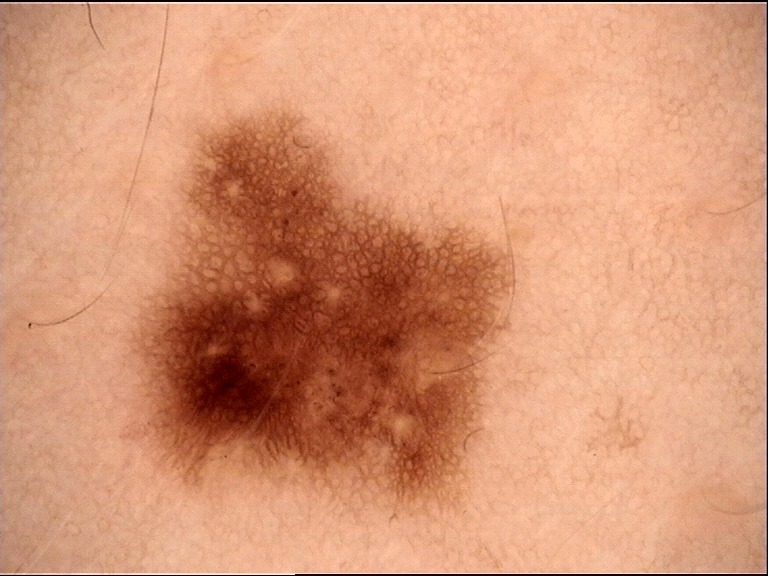A skin lesion imaged with a dermatoscope. Classified as a benign lesion — a dysplastic junctional nevus.